A dermoscopic close-up of a skin lesion: 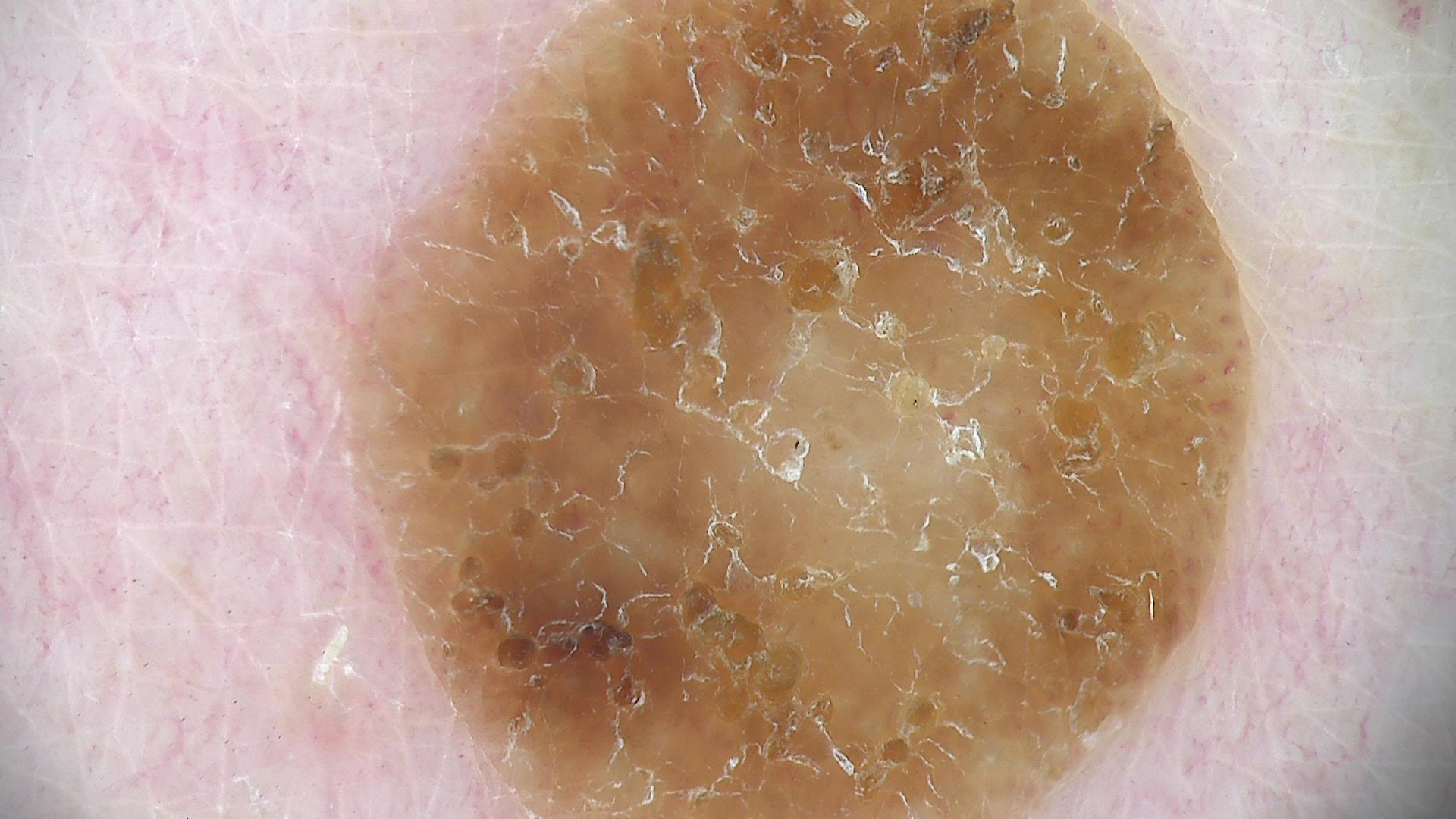The architecture is that of a keratinocytic lesion. Classified as a benign lesion — a seborrheic keratosis.